Fitzpatrick phototype IV; lay graders estimated Monk Skin Tone 2–3. Close-up view. The subject is female. Associated systemic symptoms include joint pain and fatigue. The contributor reports the lesion is raised or bumpy. Symptoms reported: burning. Located on the back of the torso. The contributor reports the condition has been present for less than one week.
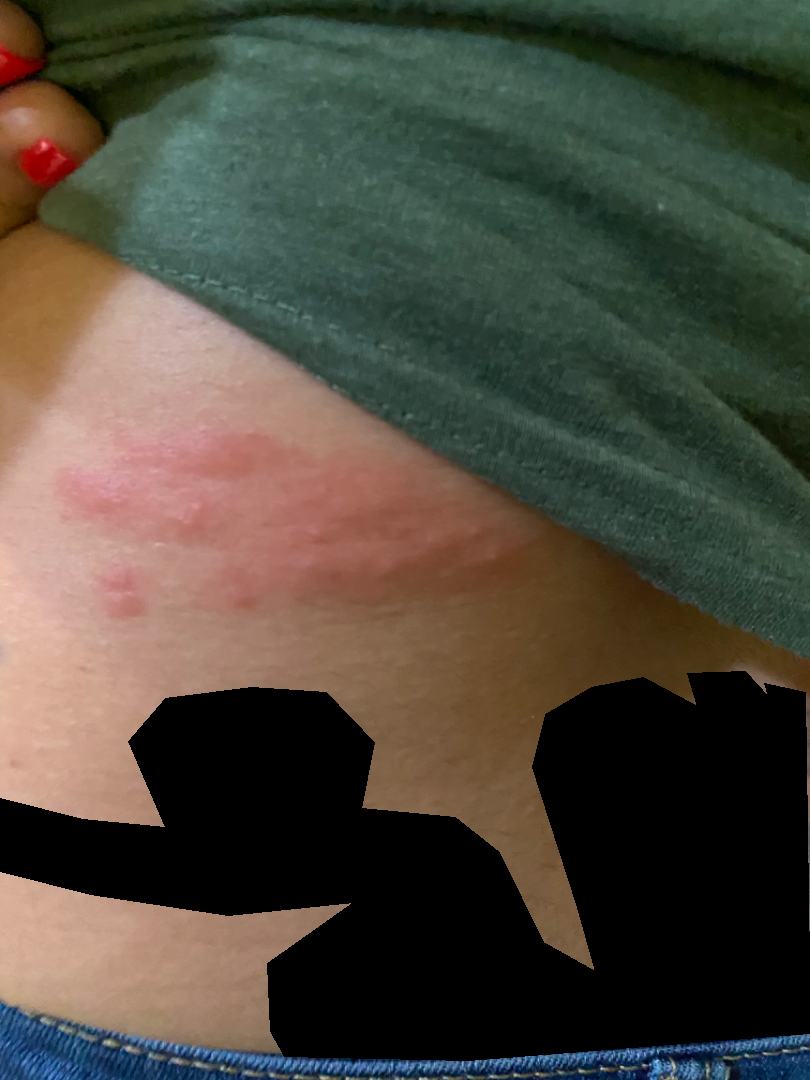| field | value |
|---|---|
| diagnostic considerations | single-reviewer assessment: in keeping with Herpes Zoster |